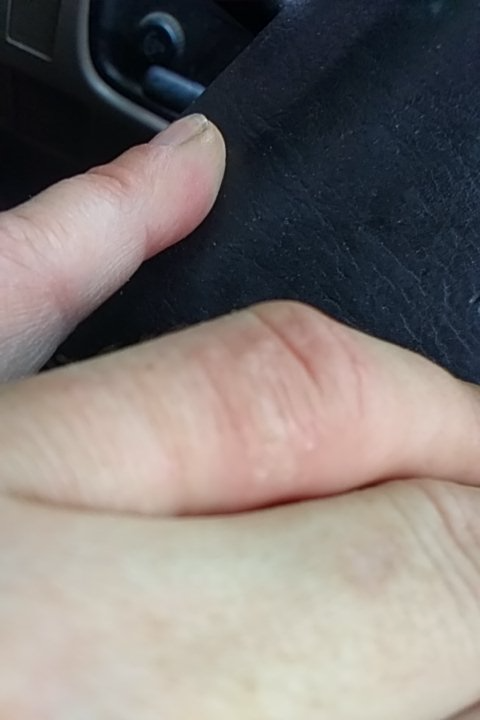Q: What was the assessment?
A: indeterminate